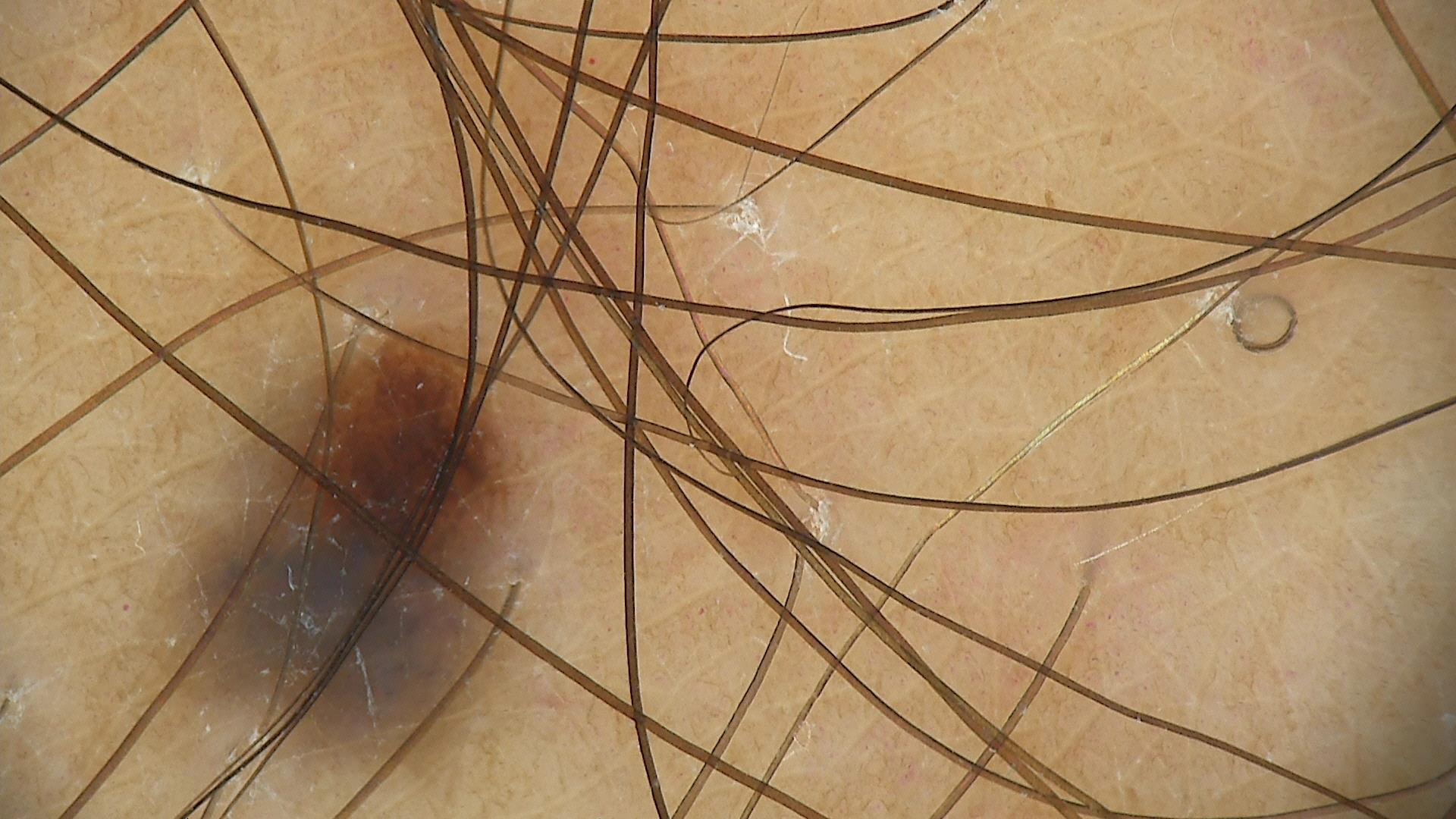category — banal; assessment — compound nevus (expert consensus).